A clinical photograph of a skin lesion. Recorded as FST II. A male patient aged 63.
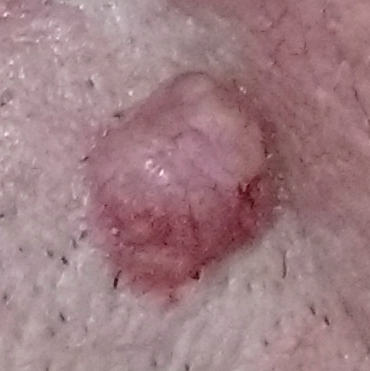symptoms: growth, elevation / no pain
diagnosis: basal cell carcinoma (biopsy-proven)